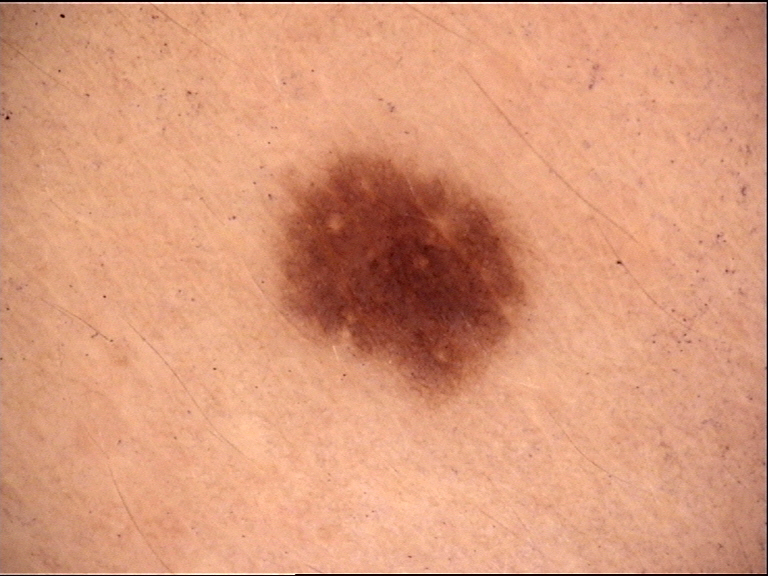Summary: A dermoscopic photograph of a skin lesion. Conclusion: Consistent with a dysplastic junctional nevus.